A female subject in their mid- to late 60s; a dermoscopic close-up of a skin lesion: 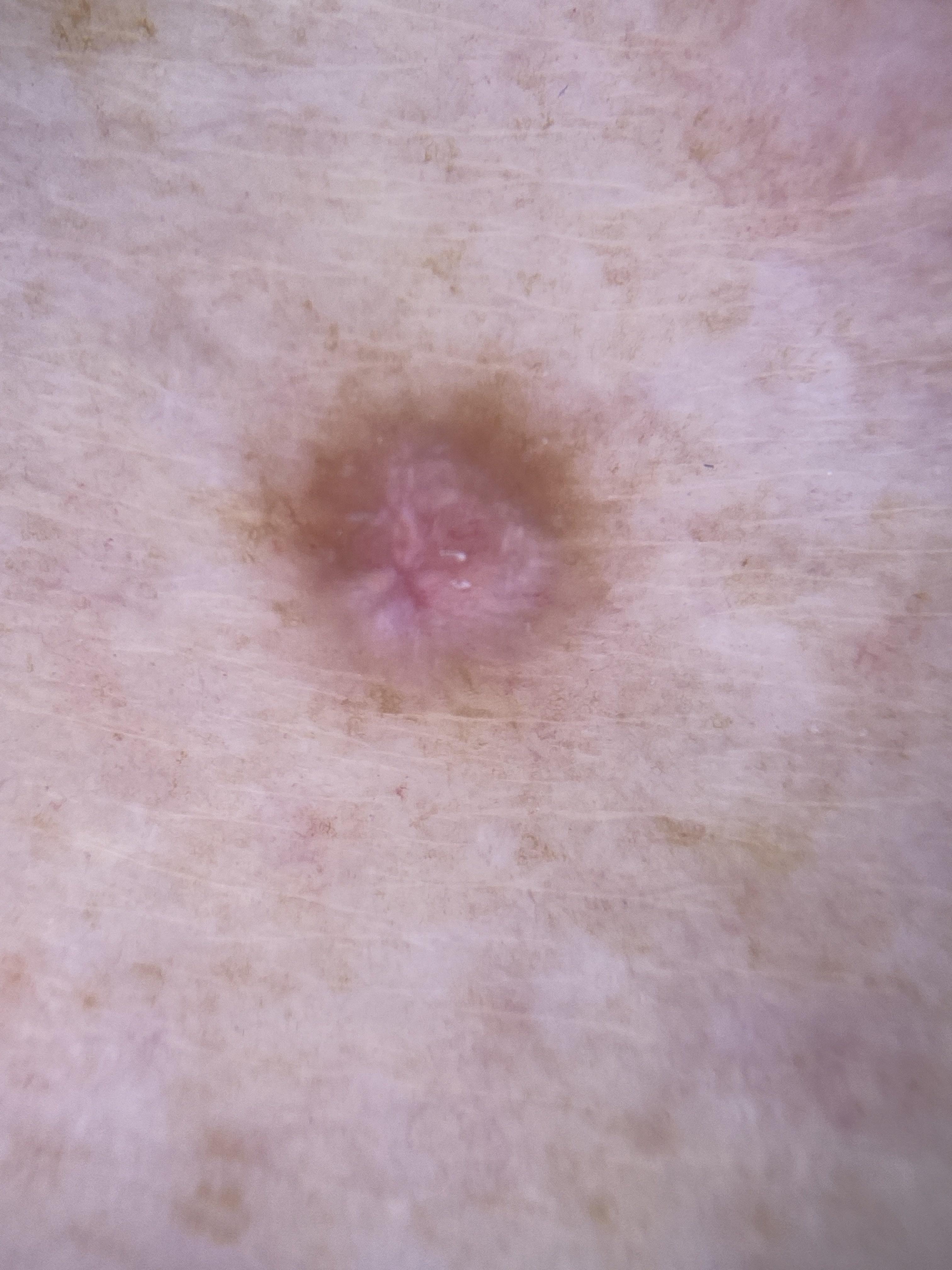The lesion is on a lower extremity.
The clinical impression was a benign lesion — a dermatofibroma.